The photograph is a close-up of the affected area:
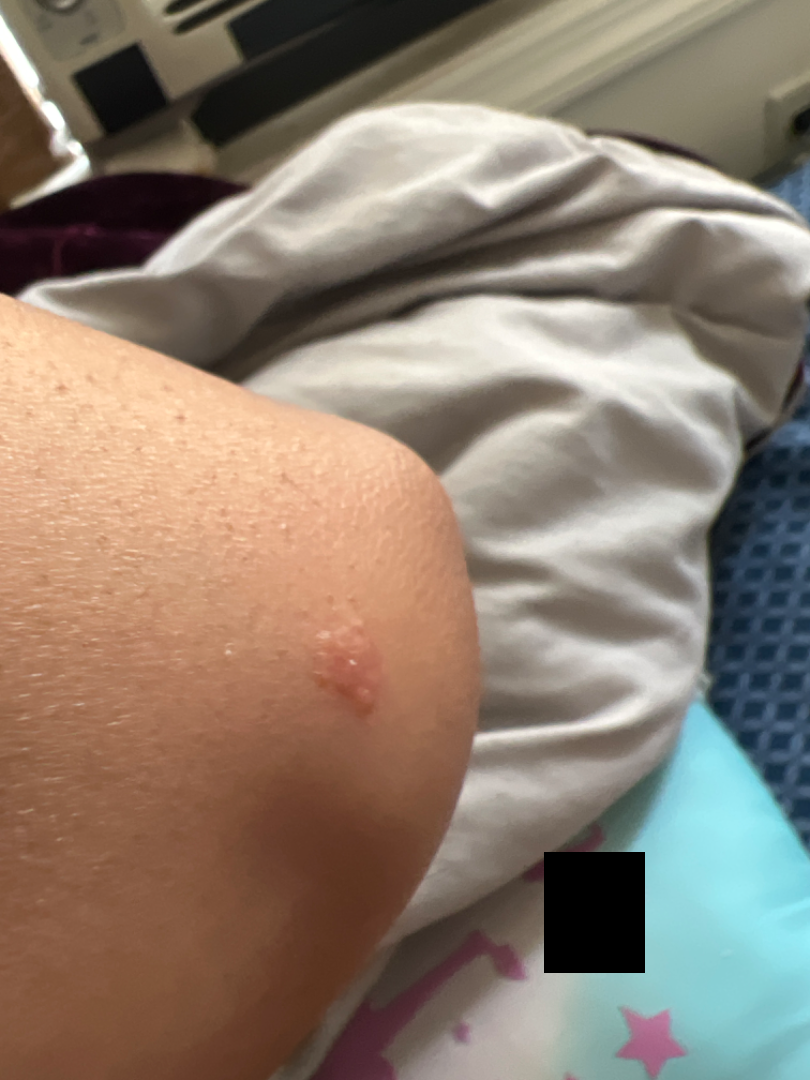Impression: The condition could not be reliably identified from the image.